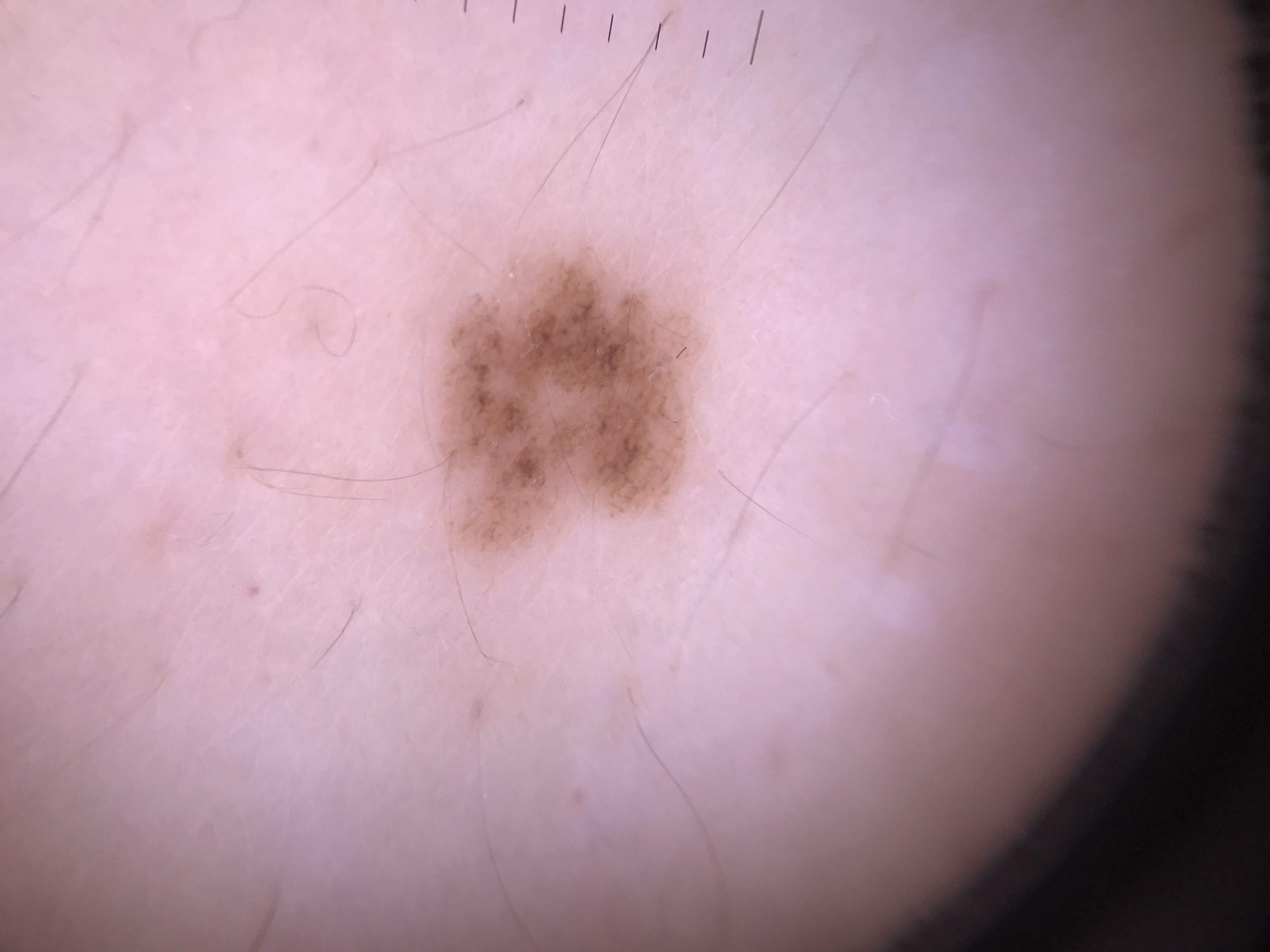Case:
– modality · dermoscopy
– diagnosis · dysplastic junctional nevus (expert consensus)